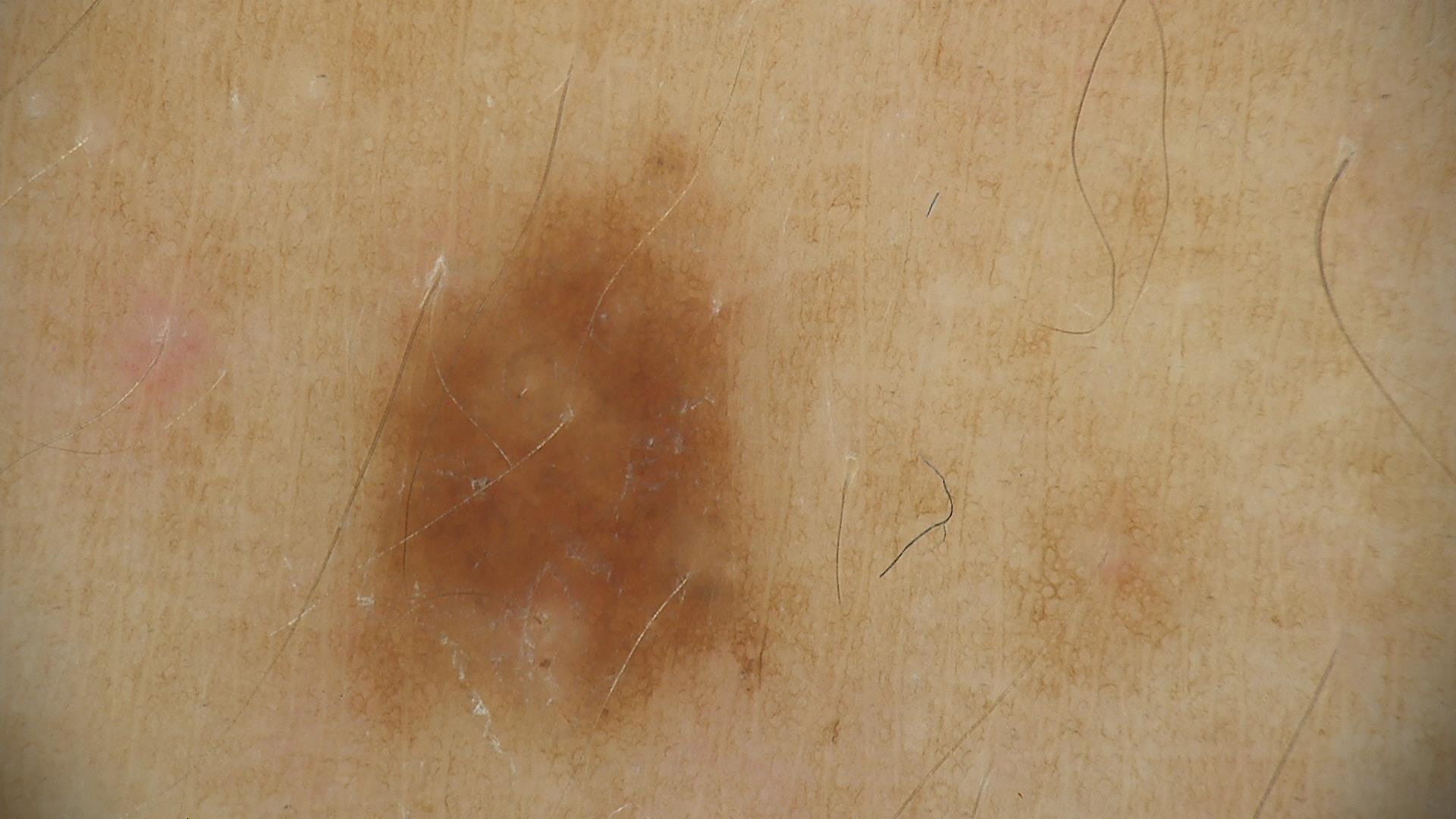A dermatoscopic image of a skin lesion. The diagnostic label was a benign lesion — a dysplastic junctional nevus.